Symptoms reported: pain, itching and enlargement; reported duration is about one day; the photograph was taken at a distance; the patient considered this a rash; the affected area is the sole of the foot, palm, back of the hand and top or side of the foot; male contributor, age 18–29:
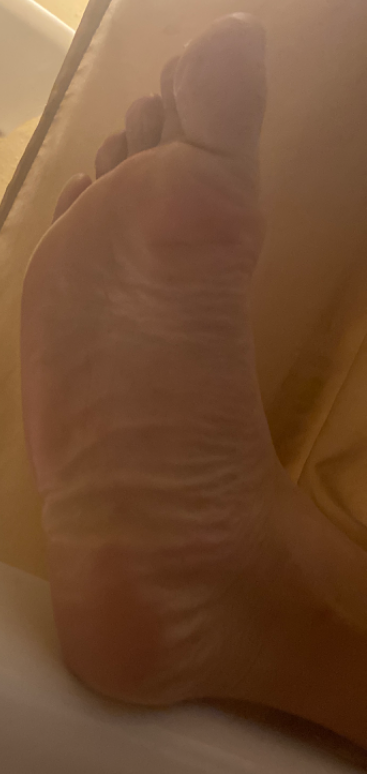No clear dermatological pathology was apparent in the photograph.